A male subject aged 83 or over · a dermoscopy image of a single skin lesion · the patient was assessed as Fitzpatrick phototype III.
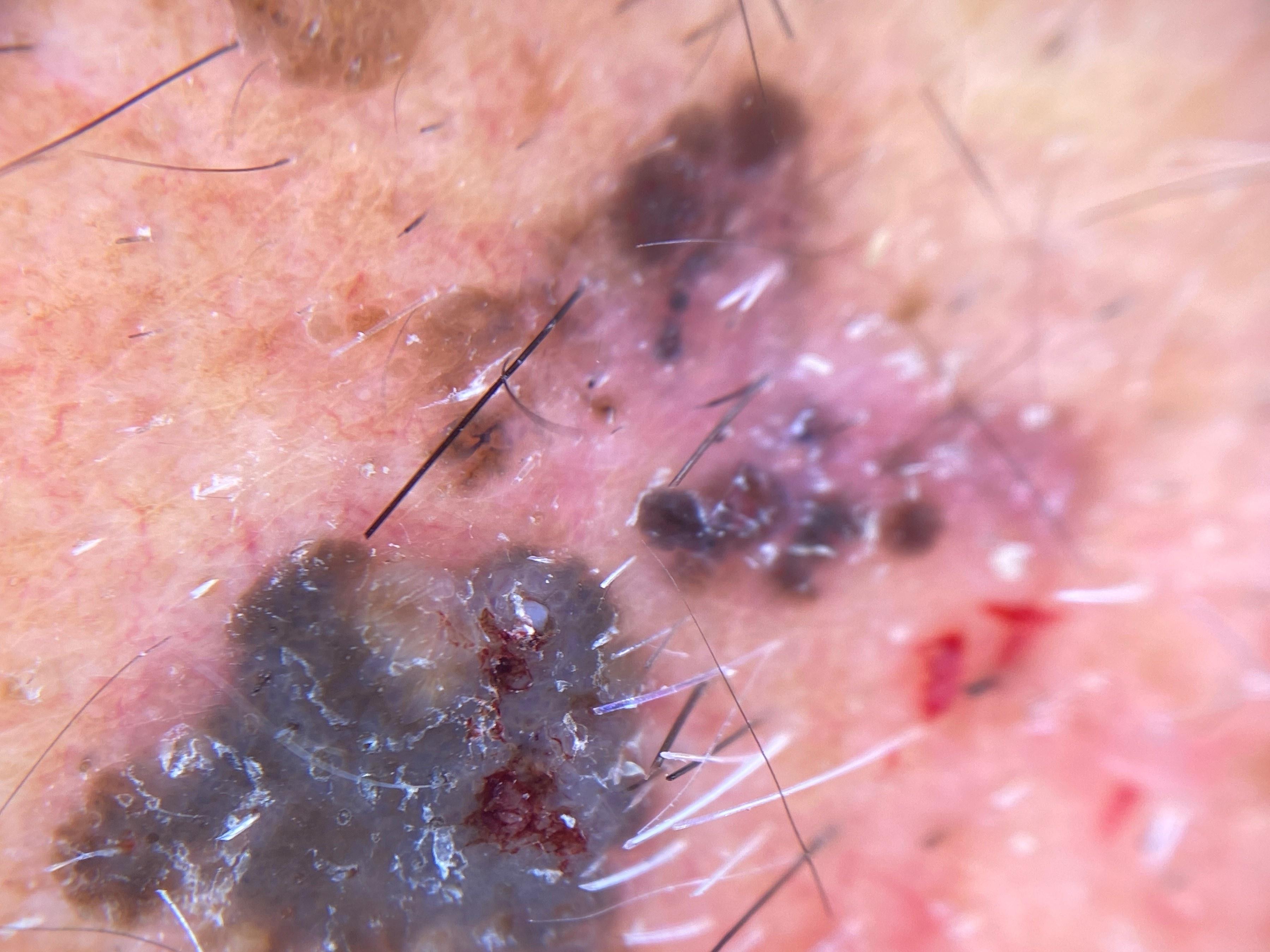Q: Where on the body is the lesion?
A: the head or neck
Q: What is this lesion?
A: Basal cell carcinoma (biopsy-proven)